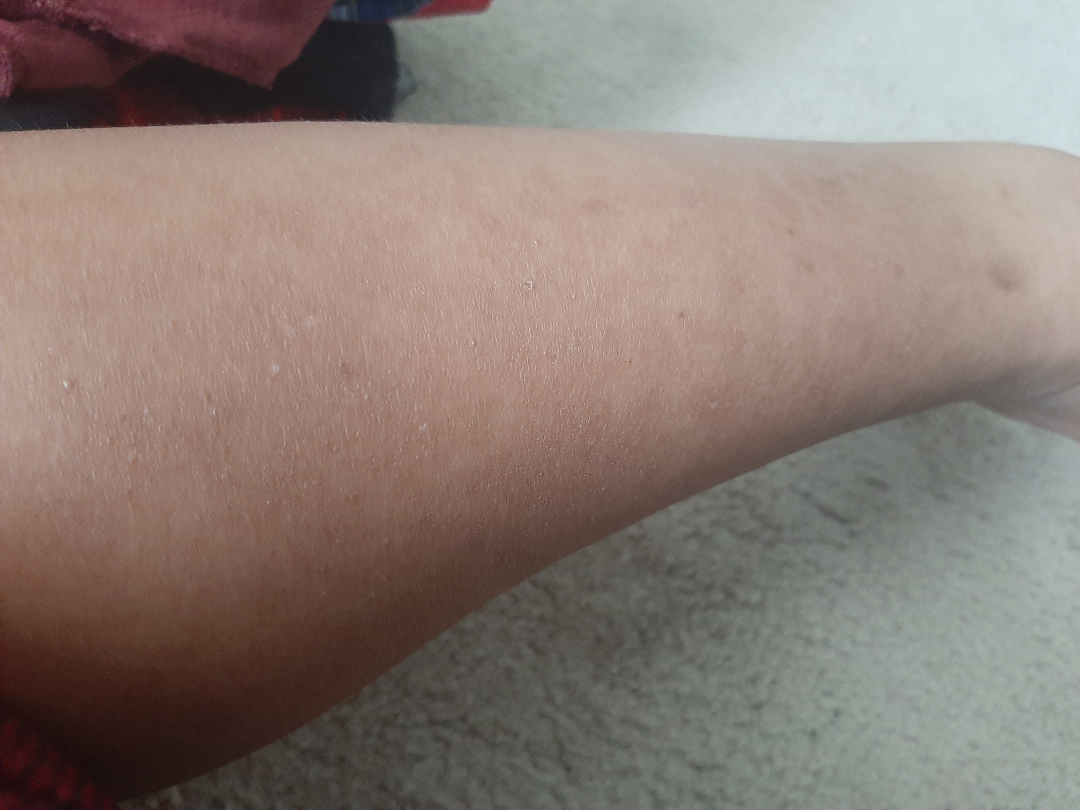The reviewing dermatologist was unable to assign a differential diagnosis from the image. This image was taken at an angle.